A contact-polarized dermoscopy image of a skin lesion · a male patient aged around 35: 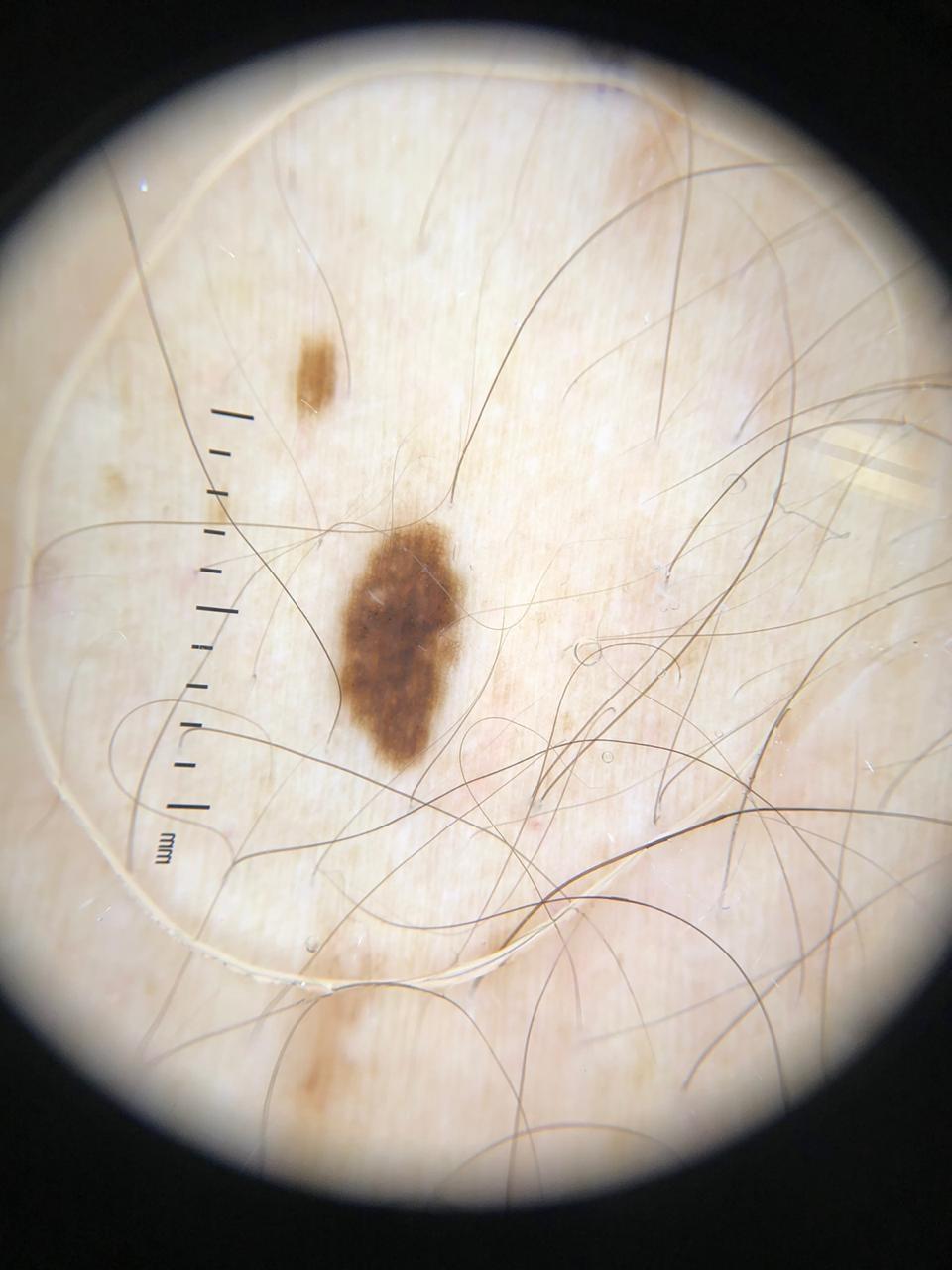The lesion was found on the trunk.
Histopathology confirmed a melanocytic lesion — a nevus.